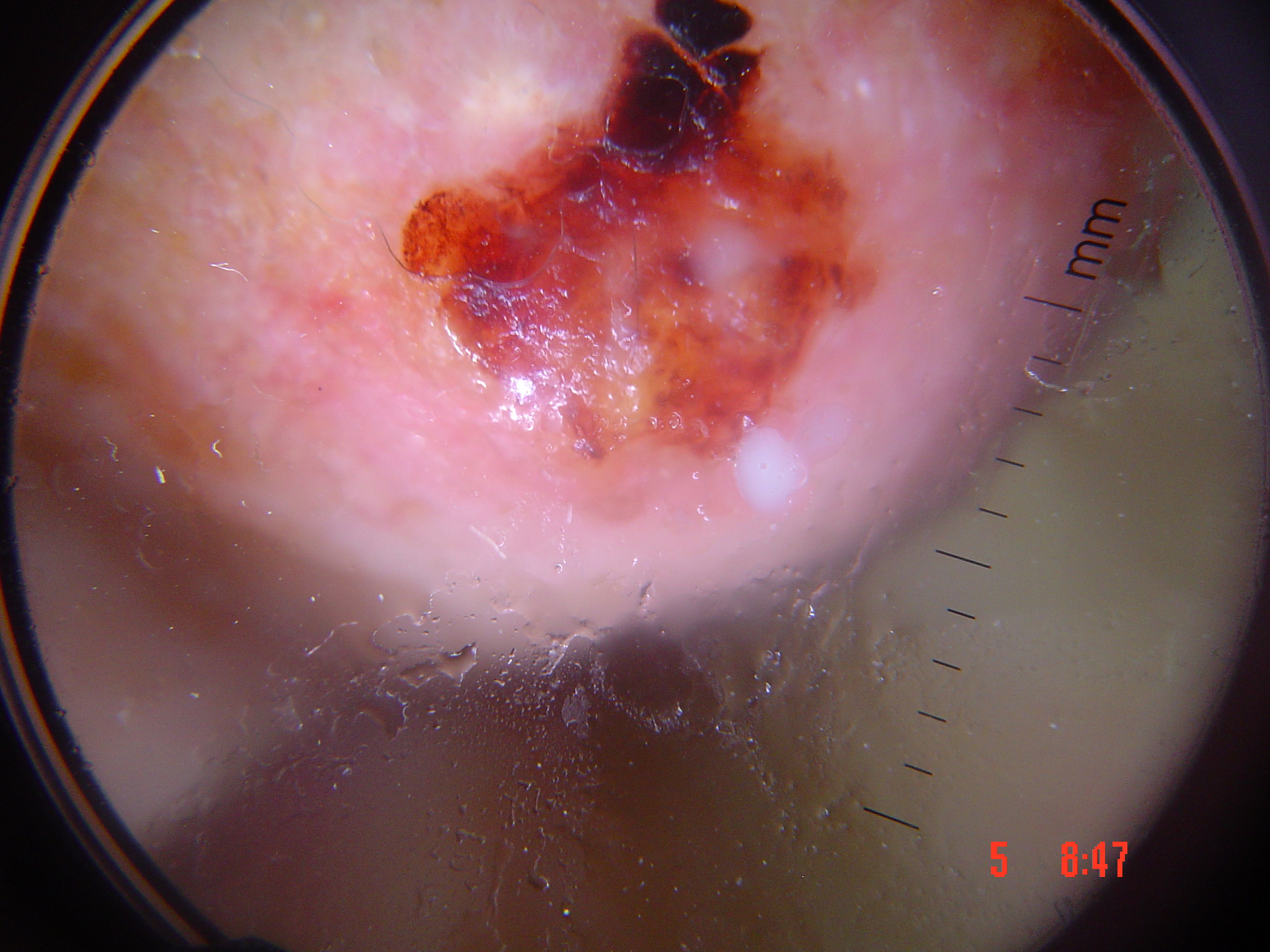class = squamous cell carcinoma (biopsy-proven).